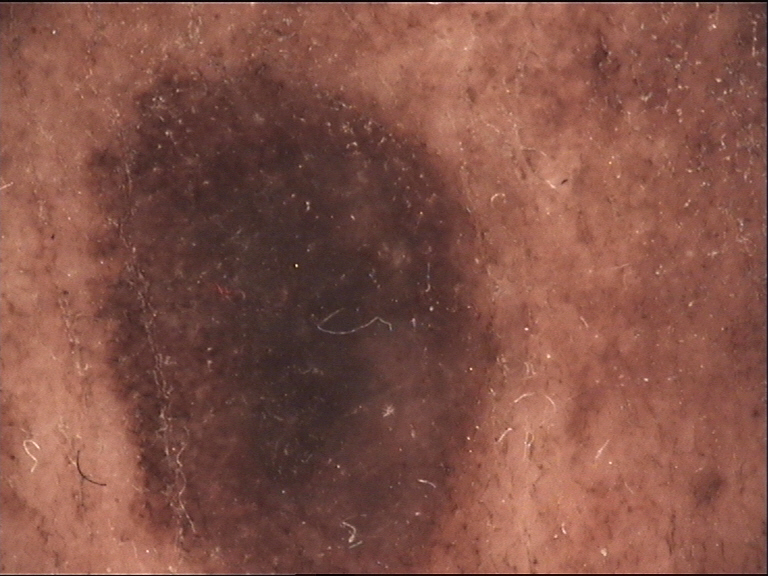The diagnosis was a congenital compound nevus.